The patient reports the condition has been present for more than five years. A close-up photograph. The affected area is the back of the hand and sole of the foot. The patient reports burning and itching. Texture is reported as fluid-filled. The subject is 40–49, male.
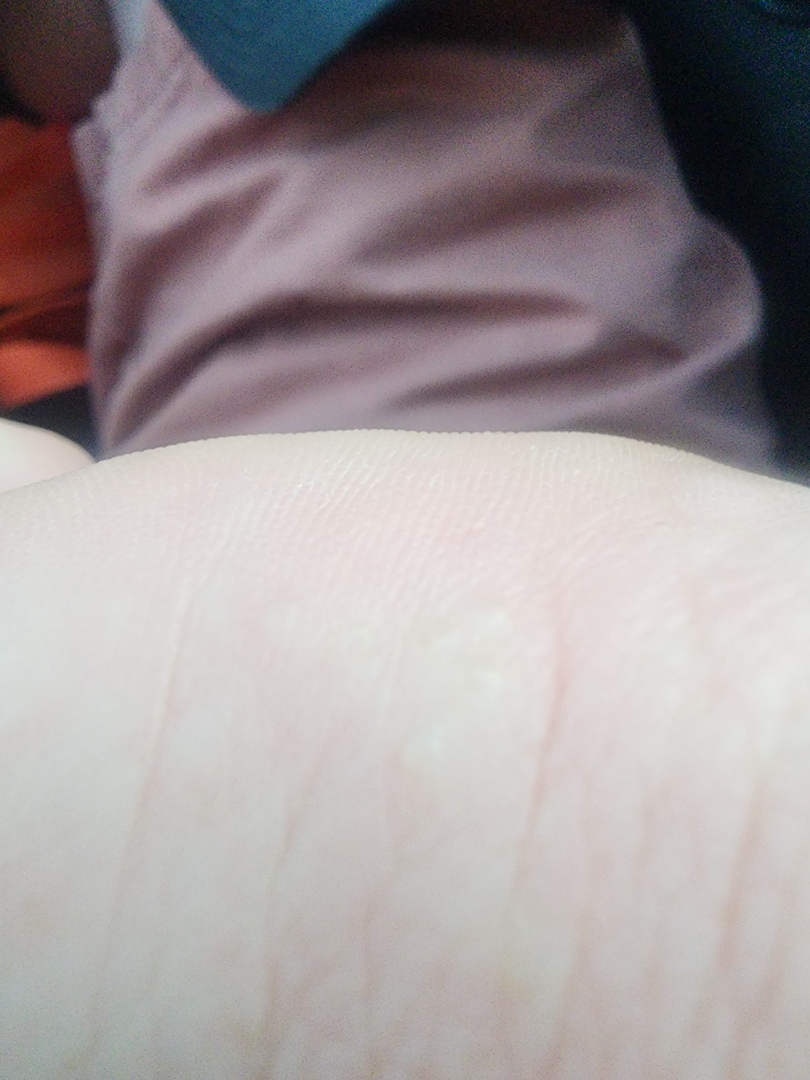Review:
The dermatologist could not determine a likely condition from the photograph alone.